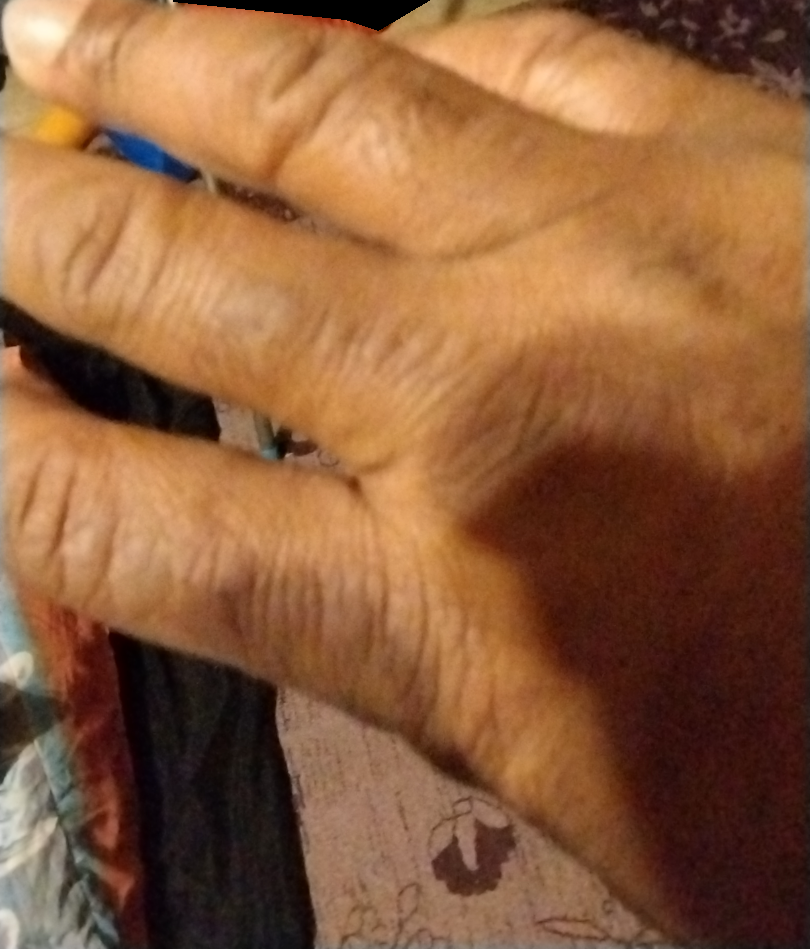Case summary:
• assessment: unable to determine
• framing: at an angle
• lesion symptoms: enlargement, burning, itching and bleeding
• other reported symptoms: none reported
• duration: three to twelve months
• site: back of the hand
• self-categorized as: a rash
• texture: raised or bumpy